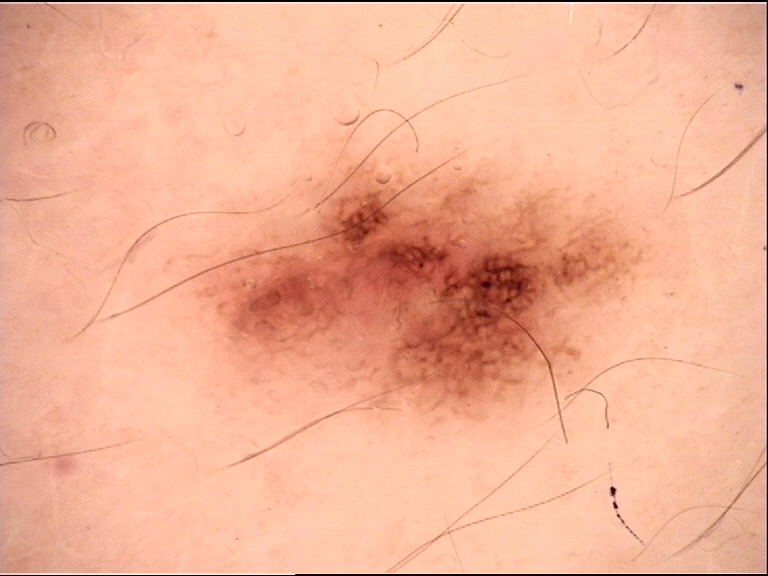- label — dysplastic junctional nevus (expert consensus)